The photograph is a close-up of the affected area. The contributor is a male aged 30–39. The affected area is the top or side of the foot and leg — 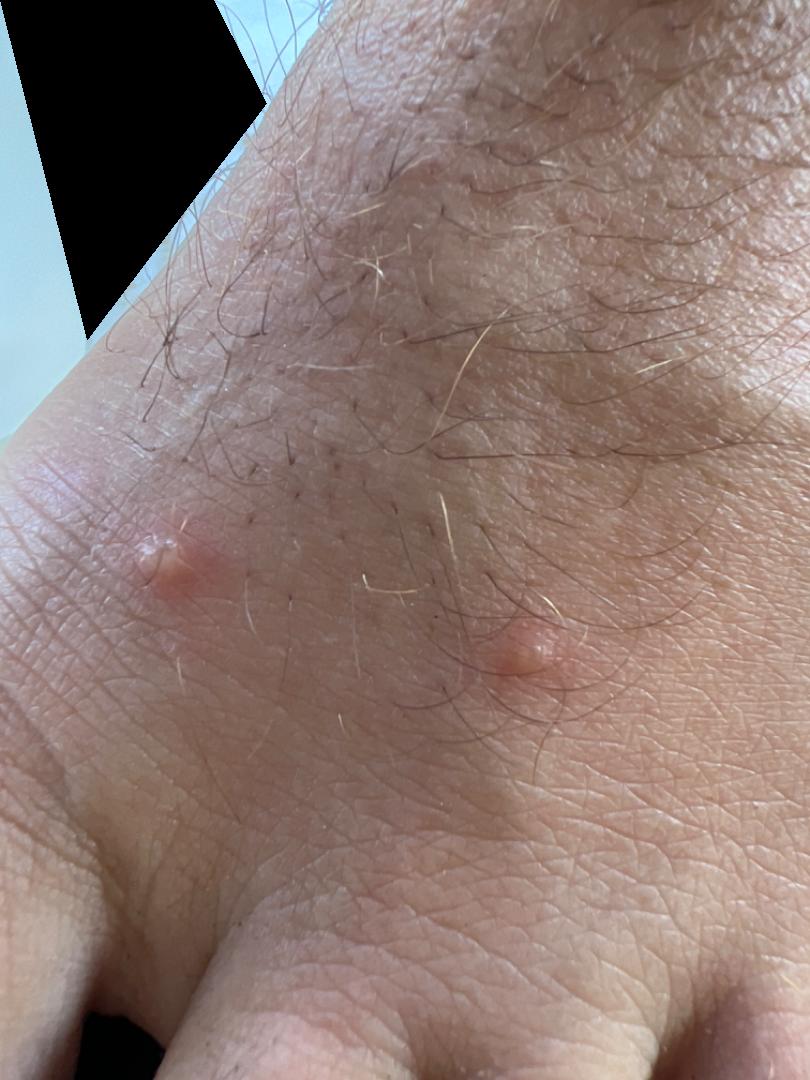clinical impression: Insect Bite (50%); Molluscum Contagiosum (50%)